A female patient, aged around 35; dermoscopy of a skin lesion: 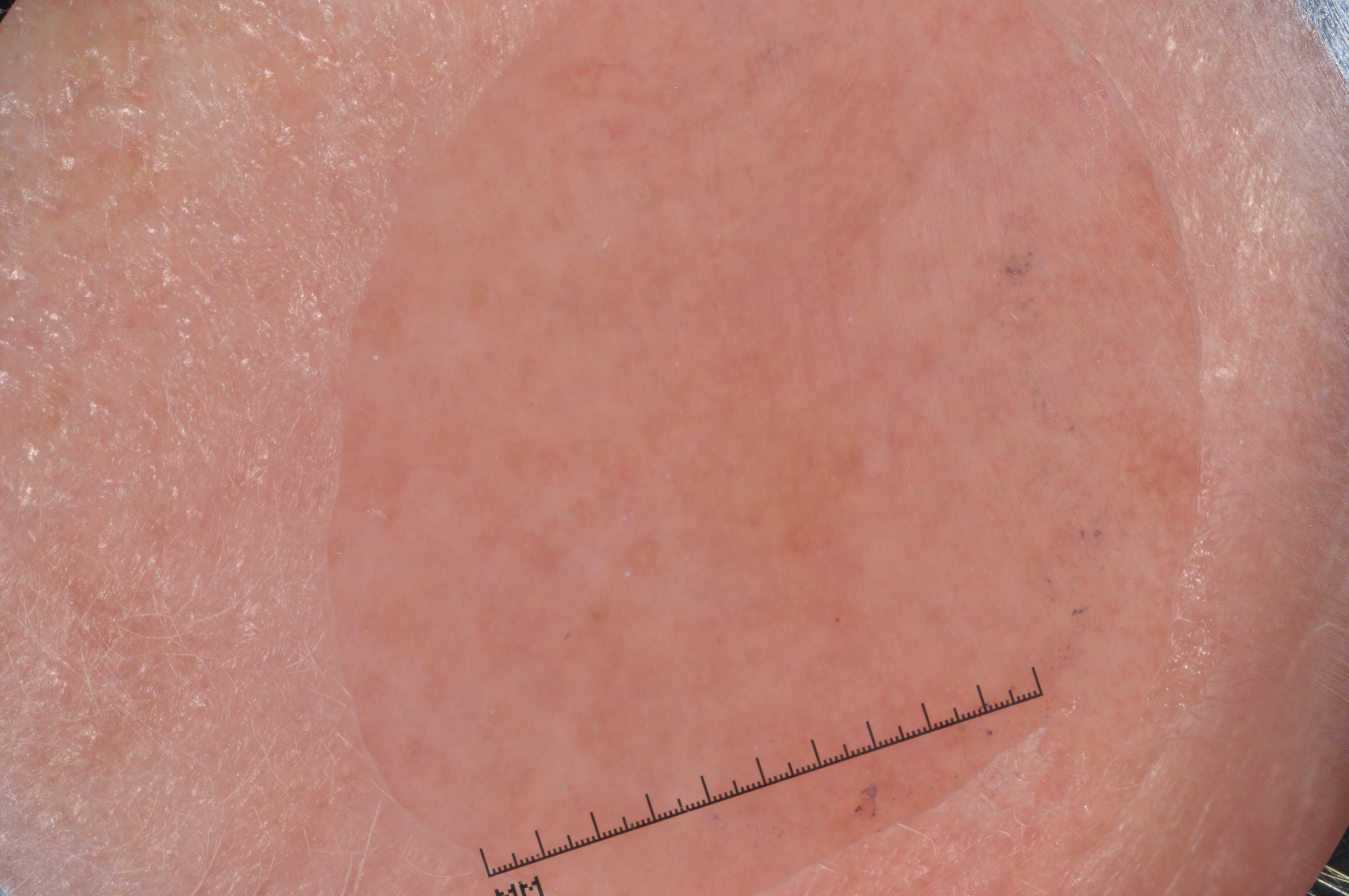Dermoscopy demonstrates no streaks, negative network, pigment network, or milia-like cysts.
As (left, top, right, bottom), the lesion spans bbox=[517, 299, 958, 633].
The clinical diagnosis was a melanocytic nevus.